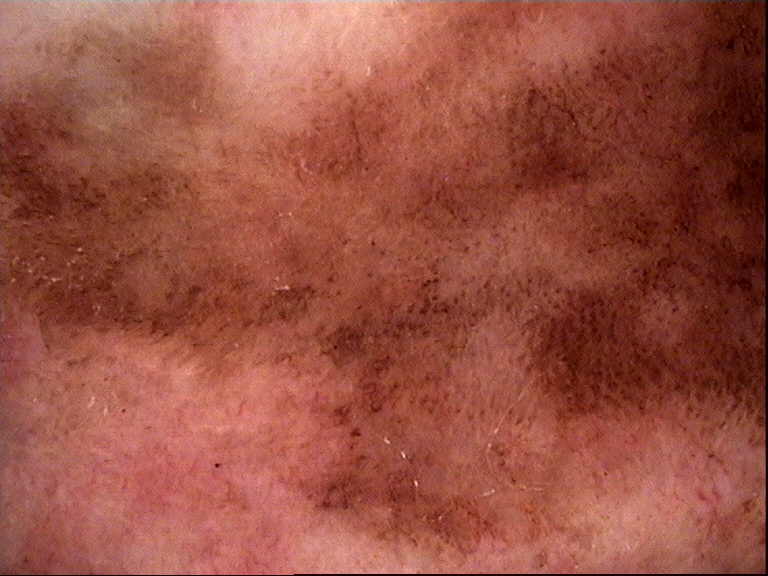Histopathologically confirmed as a keratinocytic lesion — Bowen's disease.